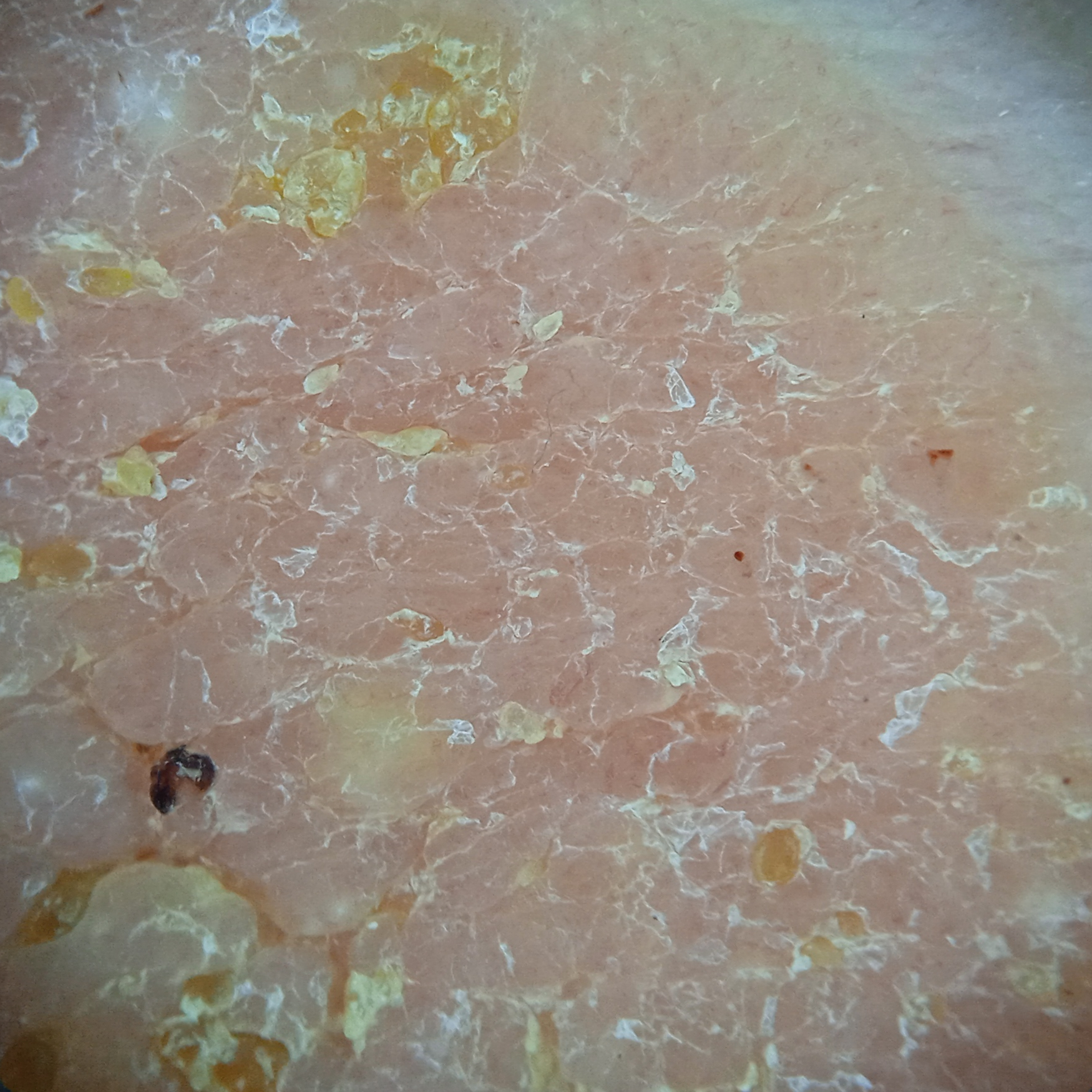Findings:
A moderate number of moles by the patient's own estimate. A female subject 81 years old. Dermoscopy of a skin lesion. The patient says their skin reddens painfully with sun exposure. Collected as part of a research study, without a referral diagnosis. The lesion measures approximately 31 mm.
Conclusion:
The lesion was assessed as a seborrheic keratosis.